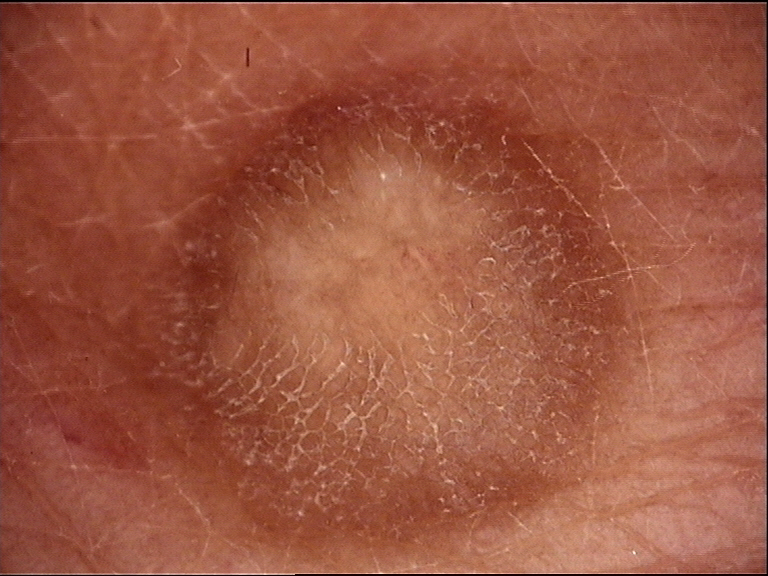Dermoscopy of a skin lesion. Classified as a fibro-histiocytic lesion — a dermatofibroma.